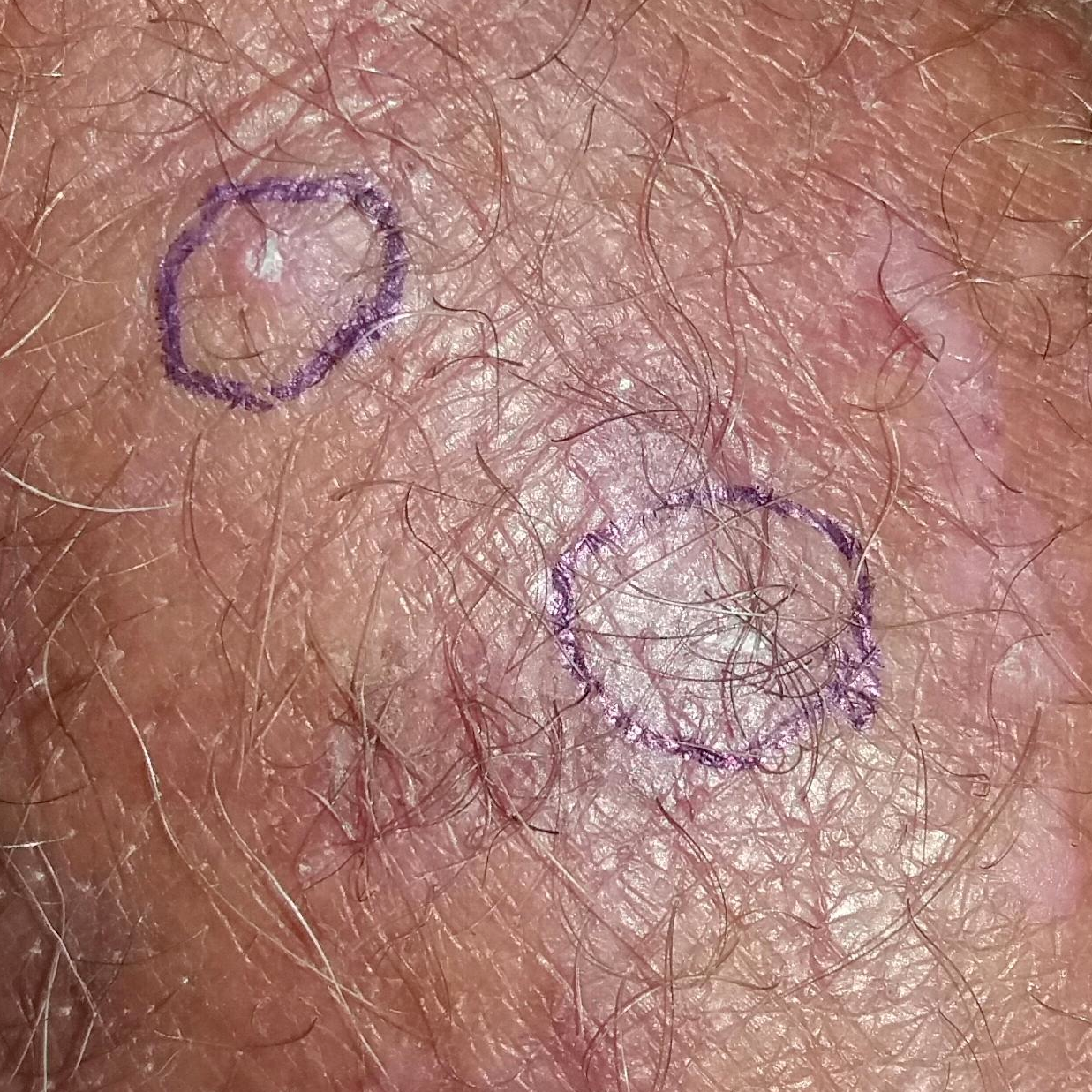Summary: A clinical photo of a skin lesion taken with a smartphone. Per patient report, the lesion itches, but has not grown and has not bled. Conclusion: Expert review favored a premalignant lesion — an actinic keratosis.